The patient described the issue as a rash; reported duration is three to twelve months; female patient, age 50–59; symptoms reported: burning, enlargement, bothersome appearance and itching; the photograph was taken at an angle; texture is reported as flat; located on the arm.
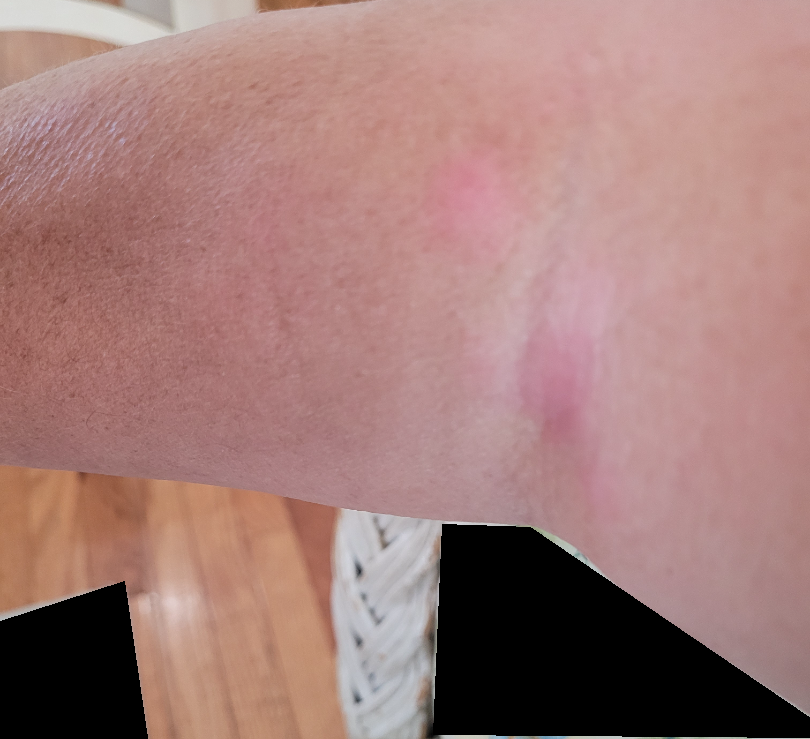Notes:
– assessment · a single dermatologist reviewed the case: the reviewer's impression was Eczema